A subject 76 years of age; a smartphone photograph of a skin lesion.
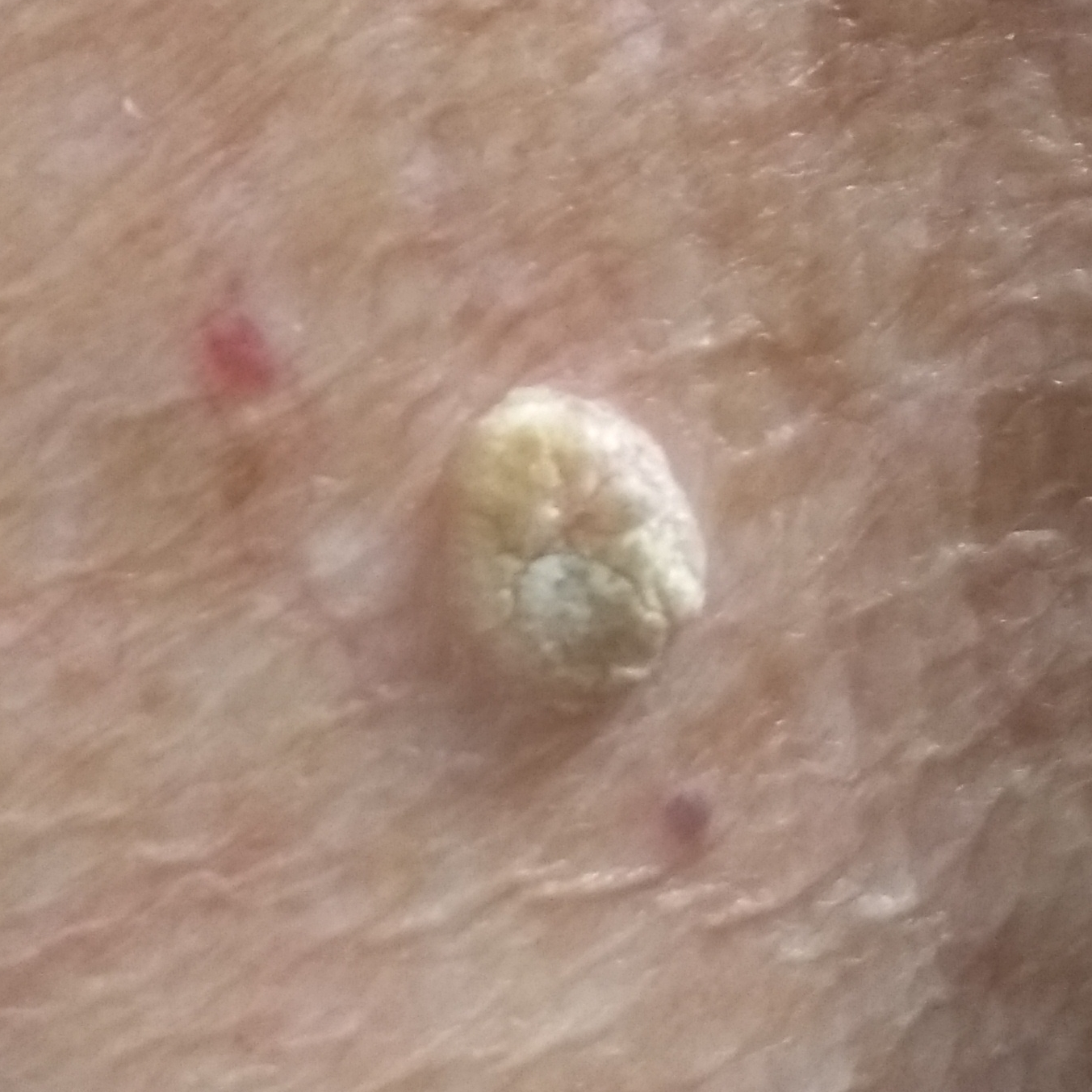Per patient report, the lesion has grown and is elevated, but has not changed and does not hurt.
Clinically diagnosed as a seborrheic keratosis.